A dermoscopic close-up of a skin lesion:
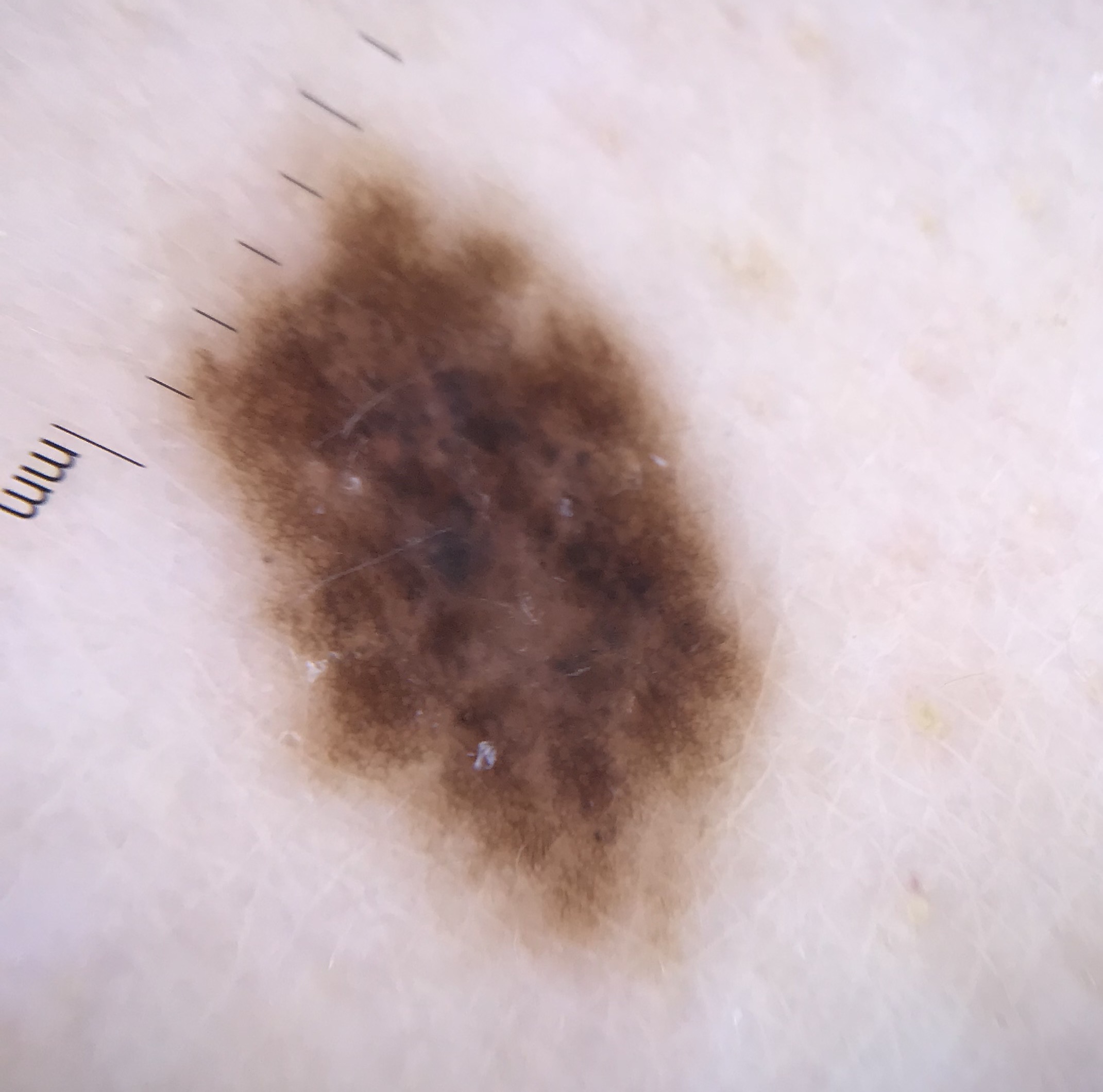Findings: This is a banal lesion. Impression: The diagnostic label was a congenital compound nevus.